Skin tone: Fitzpatrick skin type IV. Reported lesion symptoms include bothersome appearance and burning. The lesion is described as rough or flaky and flat. The subject is 30–39, female. Reported duration is about one day. The patient reported no systemic symptoms. Located on the leg. This is a close-up image: 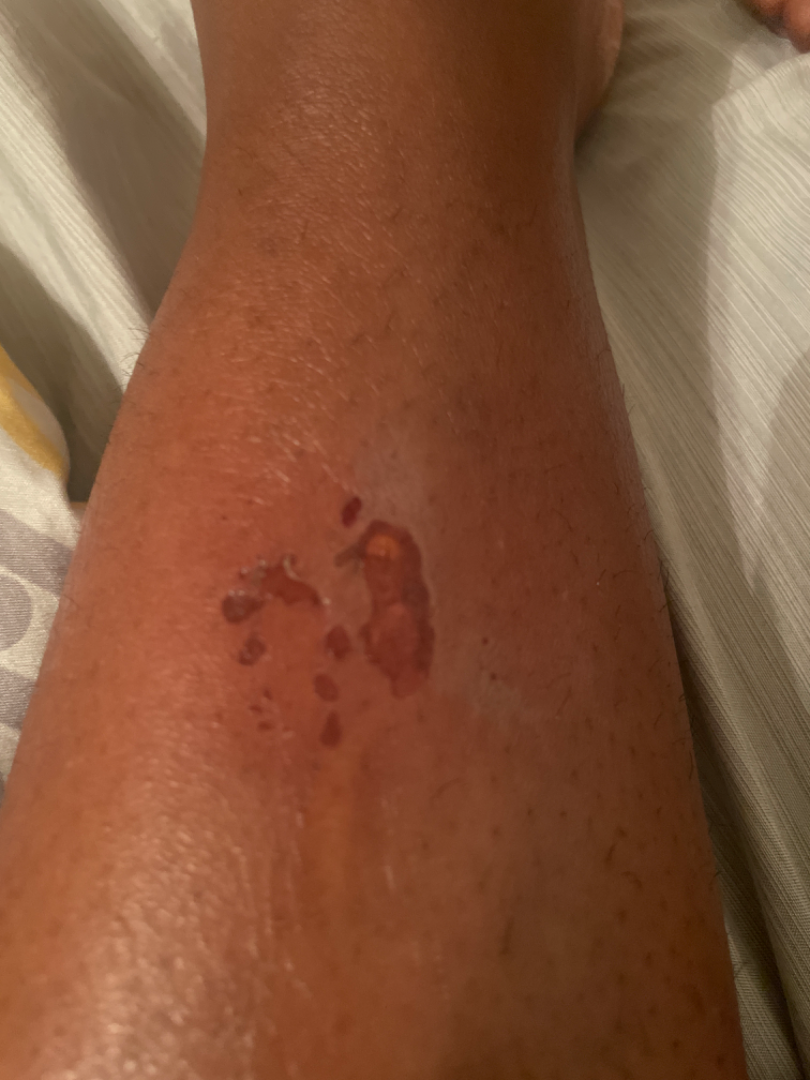Stasis Dermatitis (possible); Abrasion, scrape, or scab (possible); Bullosis diabeticorum (unlikely); Allergic Contact Dermatitis (unlikely).